Close-up view, the subject is a female aged 18–29, located on the leg and arm — 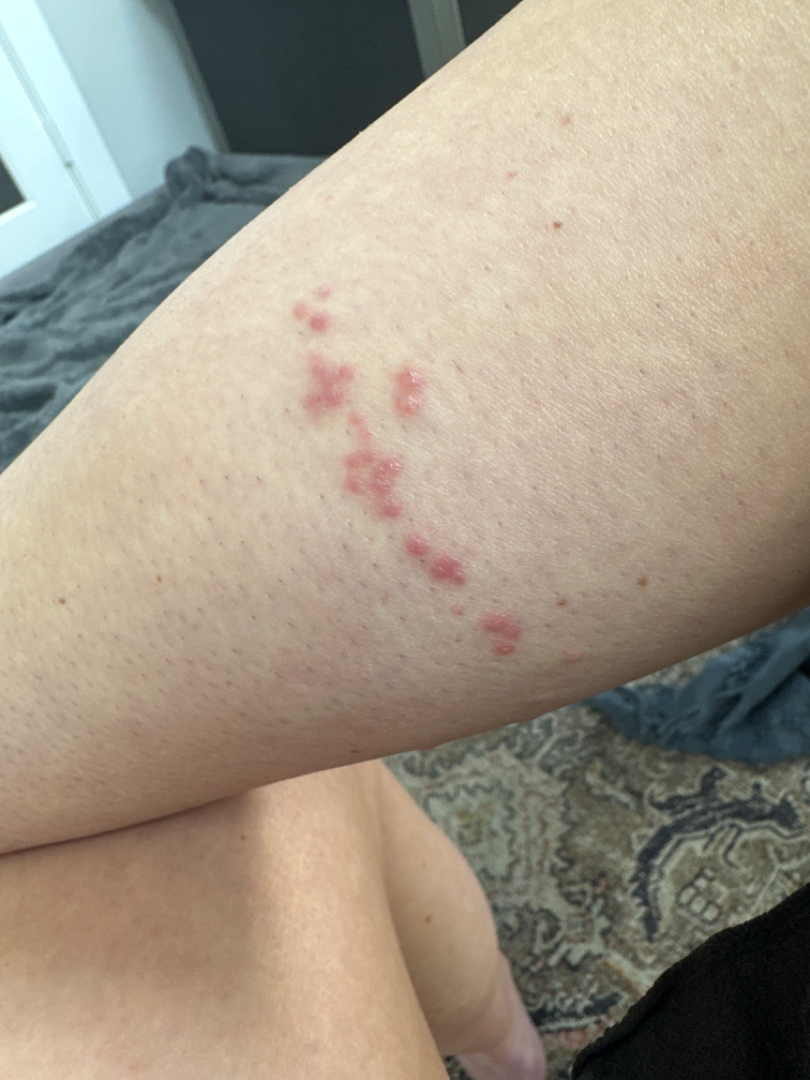The case was indeterminate on photographic review.